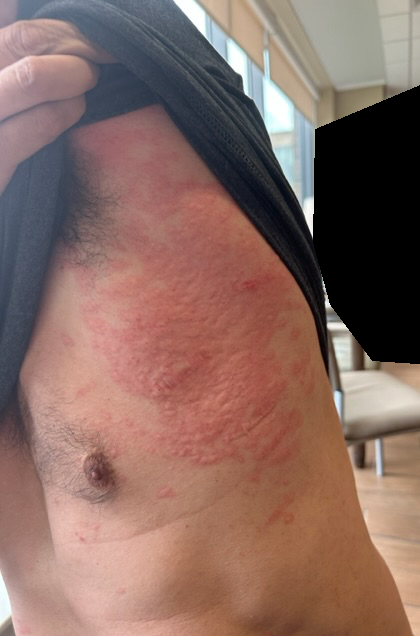<report>
<patient>male</patient>
<duration>more than one year</duration>
<symptoms>itching, pain, enlargement, burning, bothersome appearance</symptoms>
<shot_type>close-up</shot_type>
<body_site>leg, front of the torso, arm, head or neck, back of the torso</body_site>
<texture>raised or bumpy, fluid-filled</texture>
<systemic_symptoms>fatigue</systemic_symptoms>
<patient_category>a rash</patient_category>
</report>